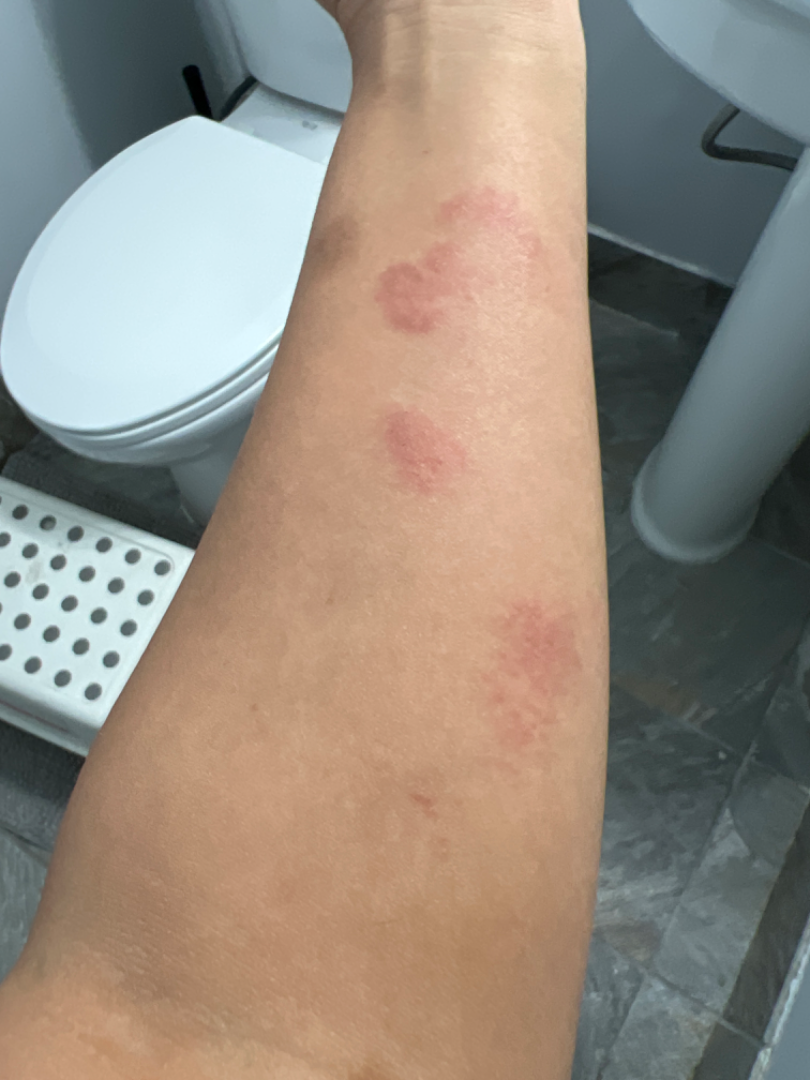<dermatology_case>
<patient>female, age 30–39</patient>
<body_site>arm</body_site>
<shot_type>close-up</shot_type>
<differential>
  <tied_lead>Eczema, Granuloma annulare</tied_lead>
  <considered>Tinea, Erythema elevatum diutinum</considered>
  <unlikely>Allergic Contact Dermatitis</unlikely>
</differential>
</dermatology_case>